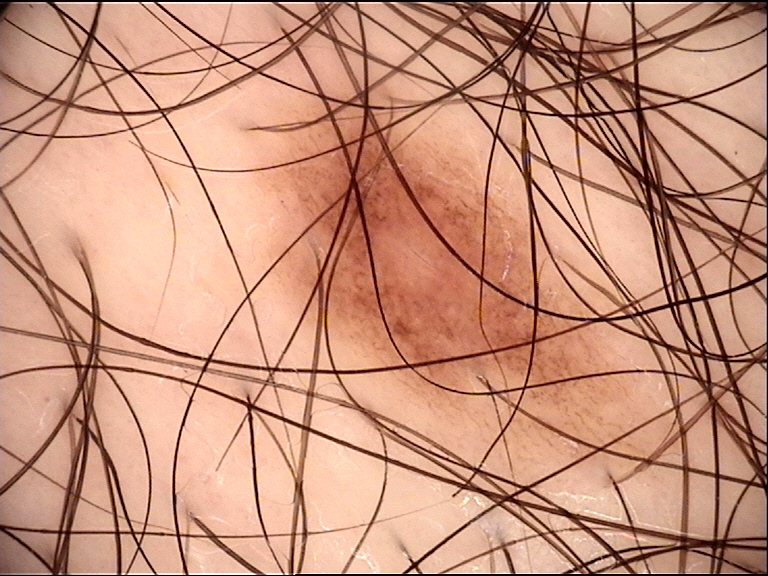Summary:
A dermoscopic close-up of a skin lesion.
Impression:
The diagnostic label was a benign lesion — a dysplastic junctional nevus.